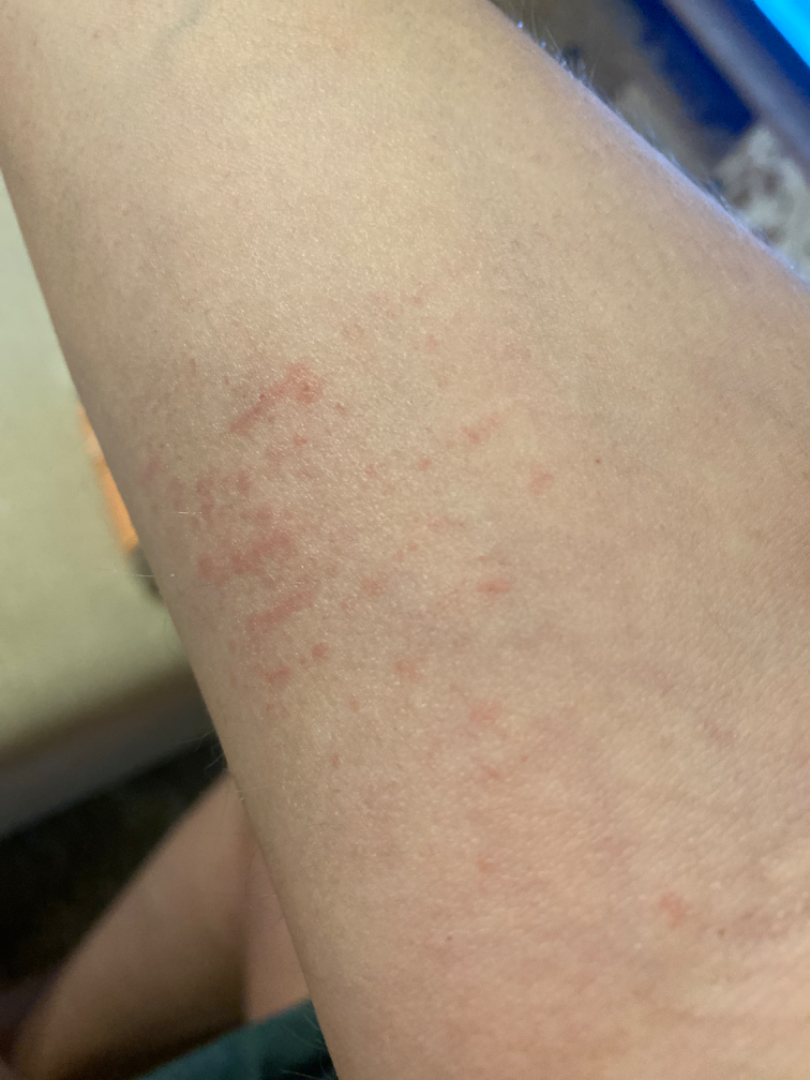patient: female, age 30–39
shot_type: close-up
body_site: arm
differential:
  leading:
    - Acute dermatitis, NOS